A dermoscopic photograph of a skin lesion.
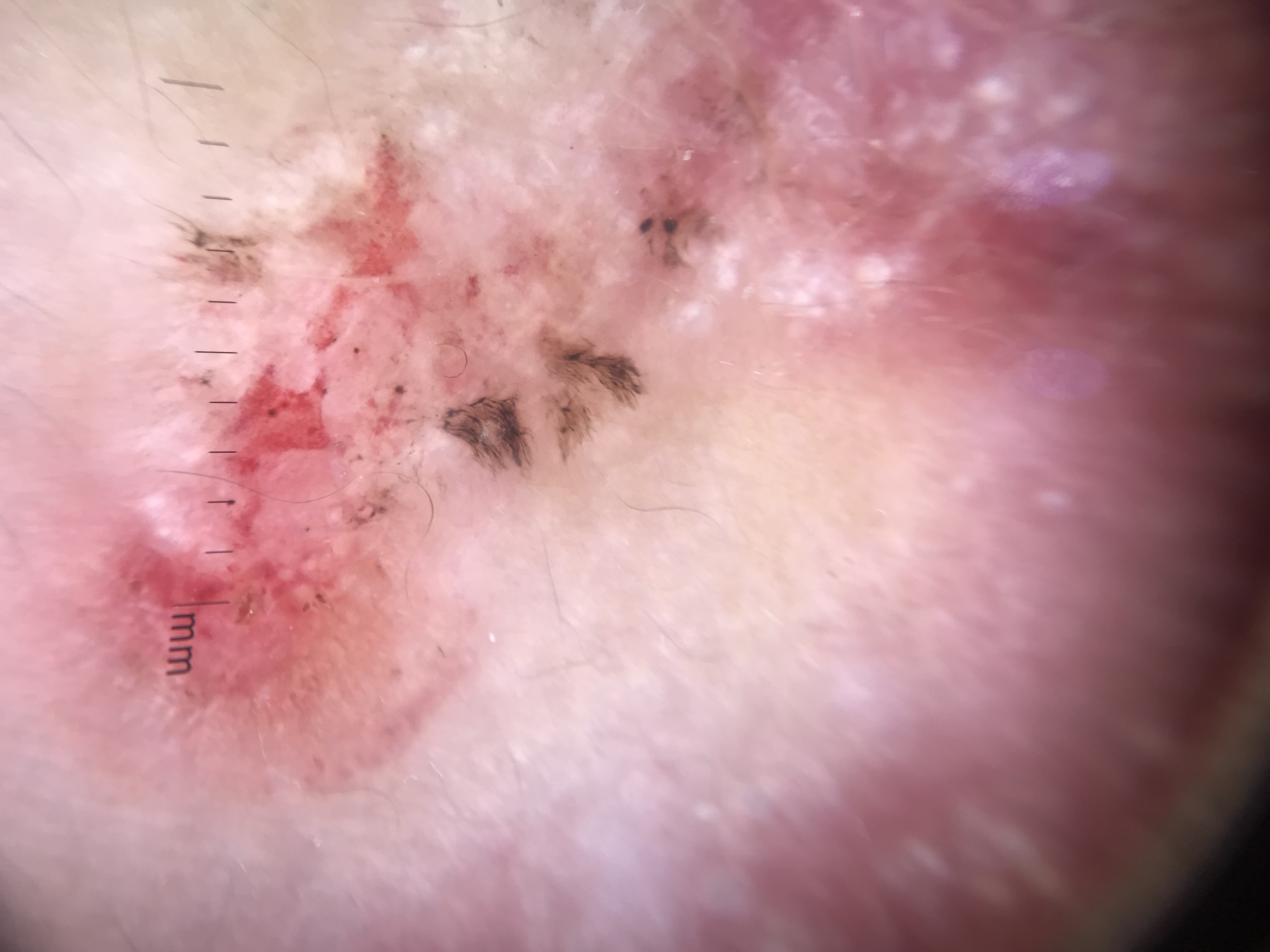Histopathology confirmed a melanoma.